A male patient 50 years old · a clinical photograph showing a skin lesion.
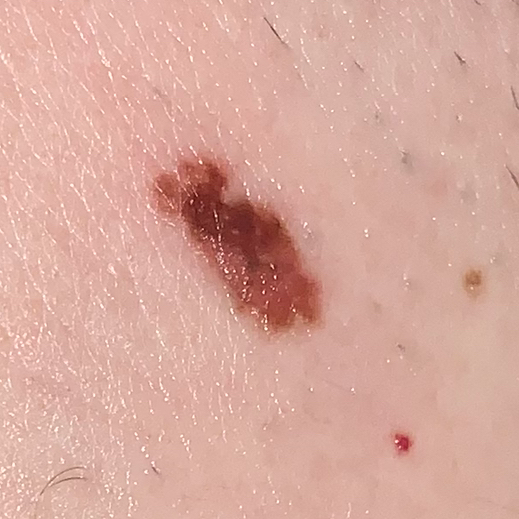The lesion is on the back. The patient reports that the lesion does not itch. Histopathologically confirmed as a nevus.